Texture is reported as raised or bumpy; self-categorized by the patient as a rash; the lesion is associated with itching; the photograph is a close-up of the affected area; the patient notes the condition has been present for less than one week; the patient is a female aged 60–69; the affected area is the leg, back of the torso, arm and palm.
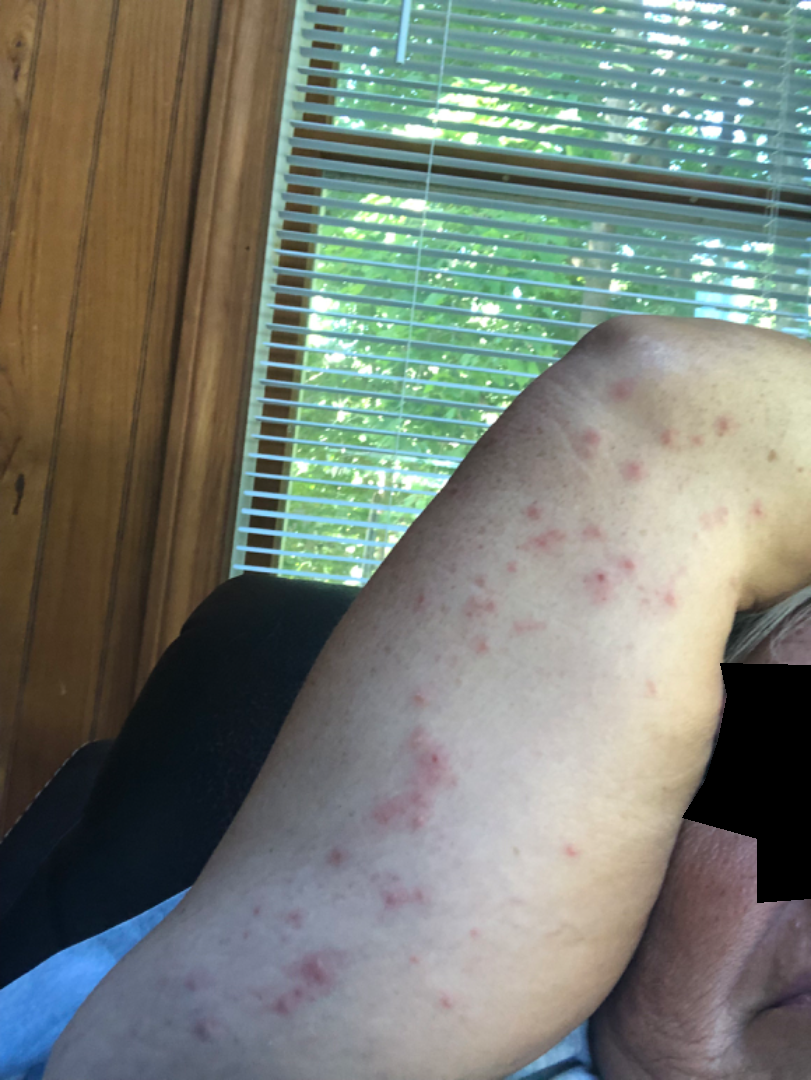On photographic review by a dermatologist, Herpes Zoster and Folliculitis were each considered, in no particular order.